Acquired for a research image collection, with no referral diagnosis · a female subject 26 years old · a clinical photograph of a skin lesion: 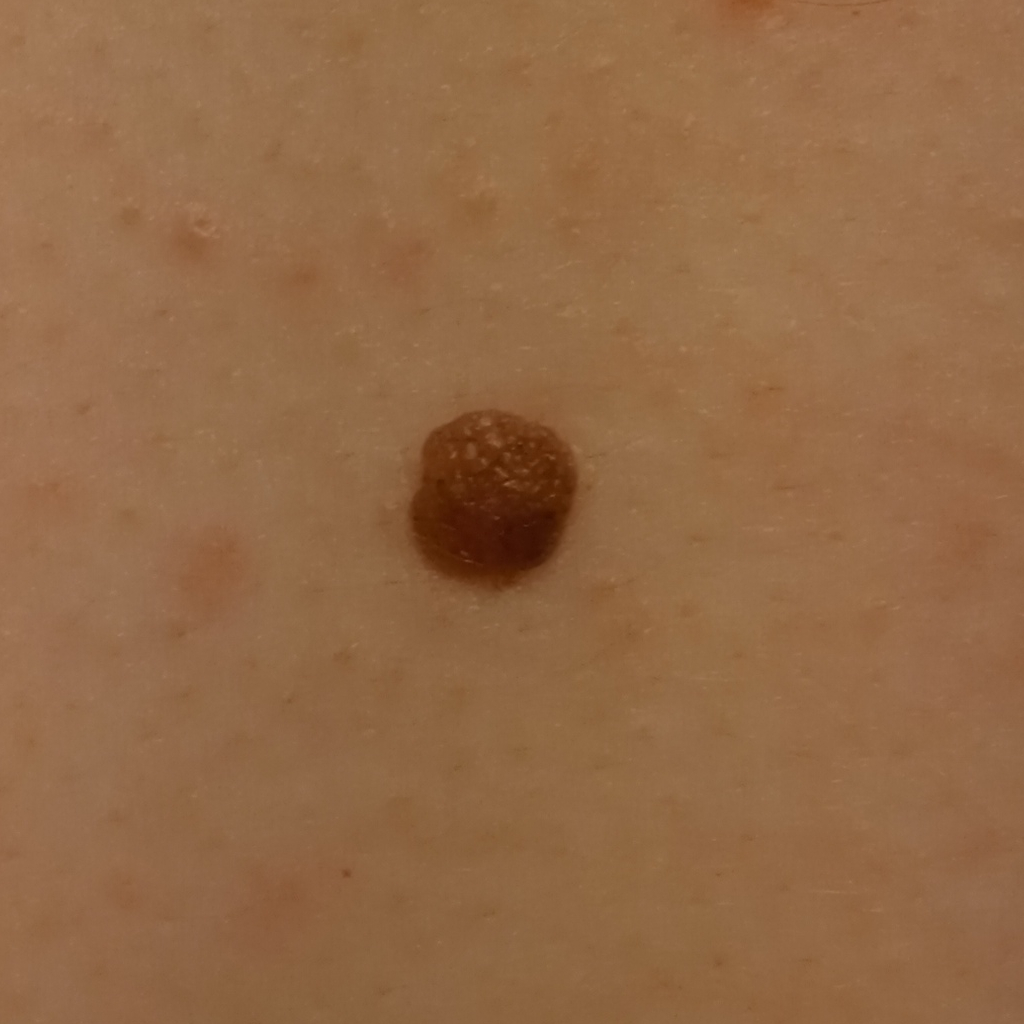{"lesion_location": "the back", "lesion_size": {"diameter_mm": 5.6}, "diagnosis": {"name": "melanocytic nevus", "malignancy": "benign"}}